A dermoscopy image of a single skin lesion: 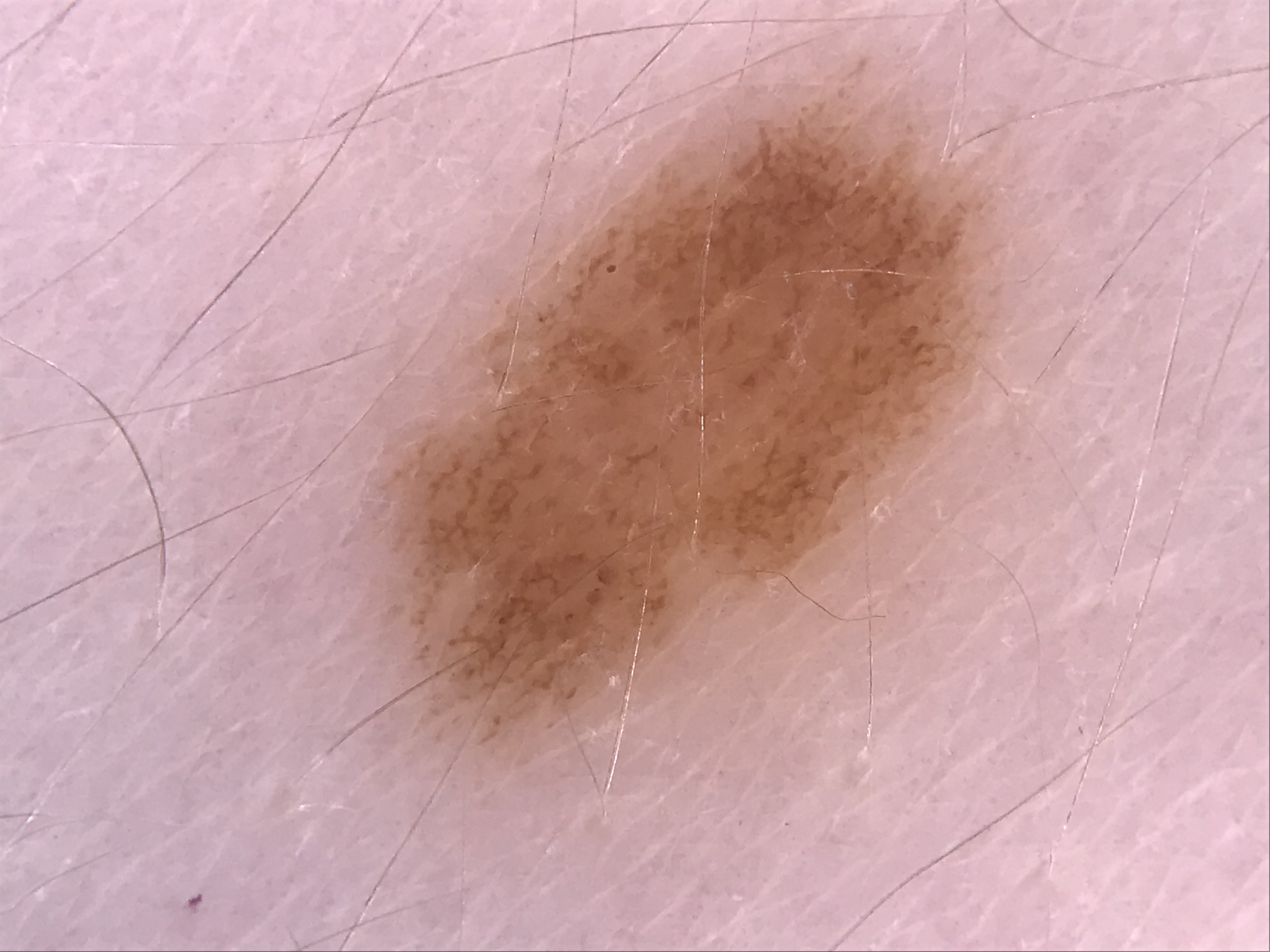assessment: dysplastic junctional nevus (expert consensus).